Dermoscopy of a skin lesion.
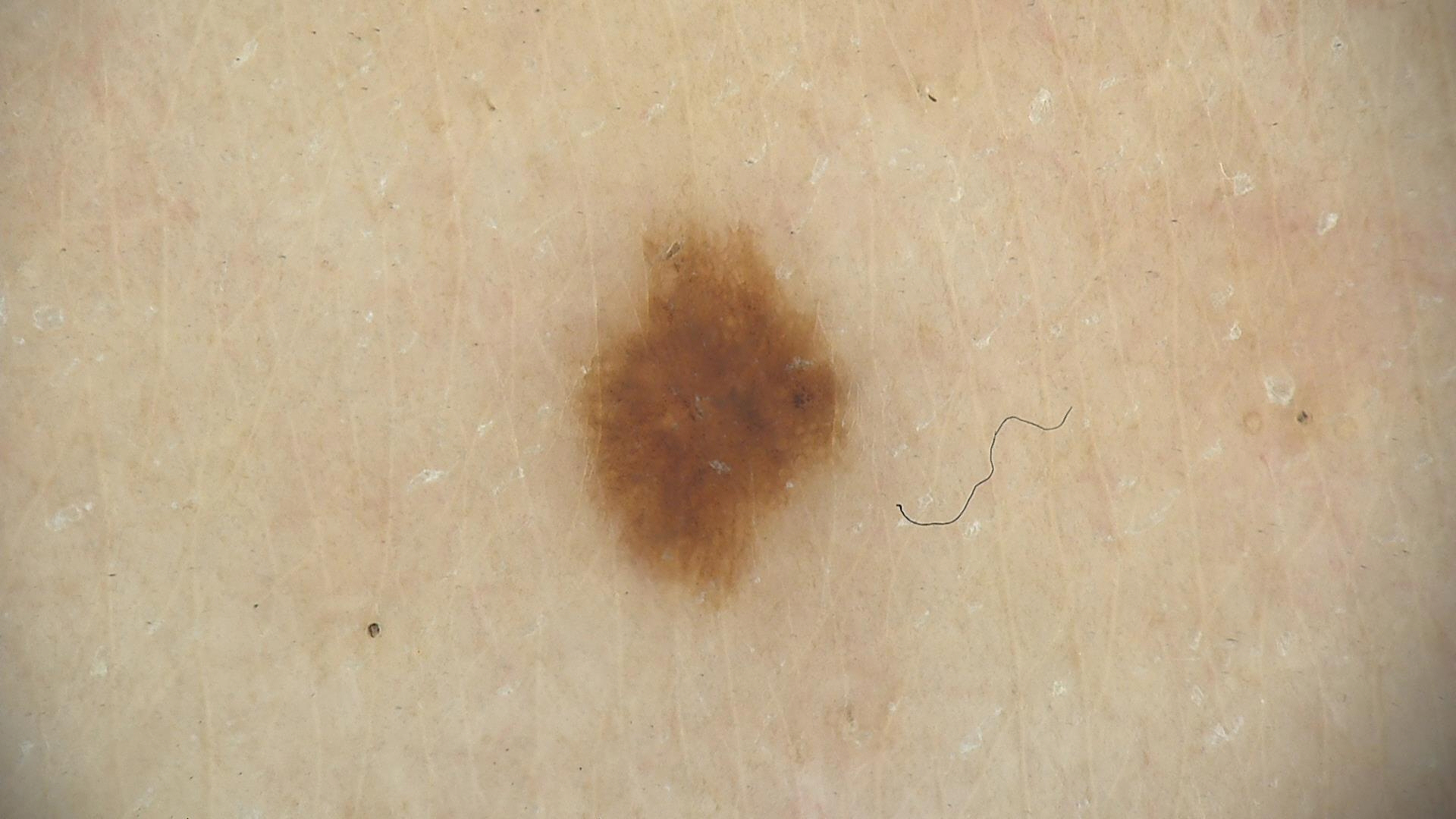Q: What was the diagnostic impression?
A: dysplastic junctional nevus (expert consensus)